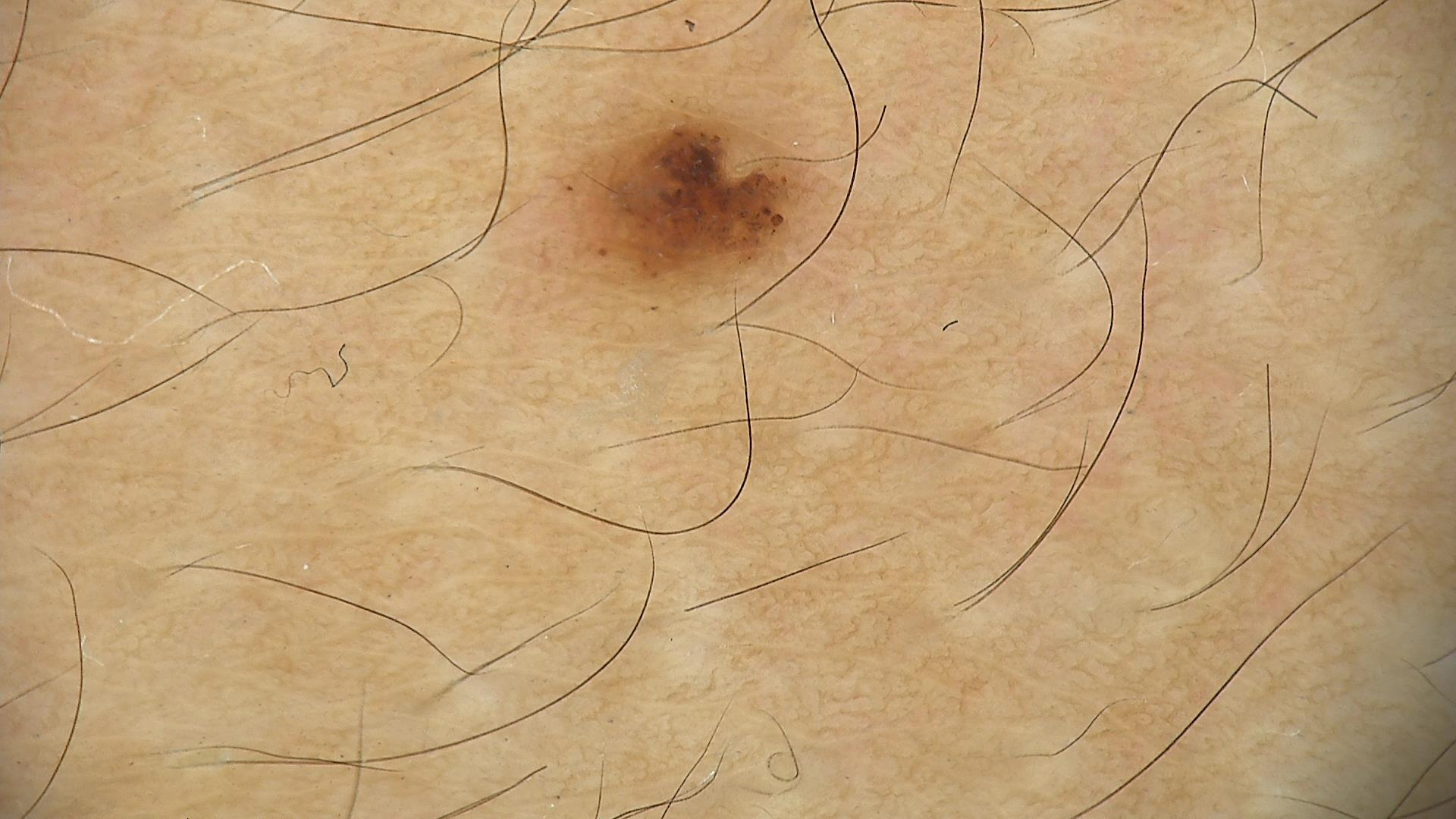A dermoscopic photograph of a skin lesion. The diagnostic label was a dysplastic junctional nevus.